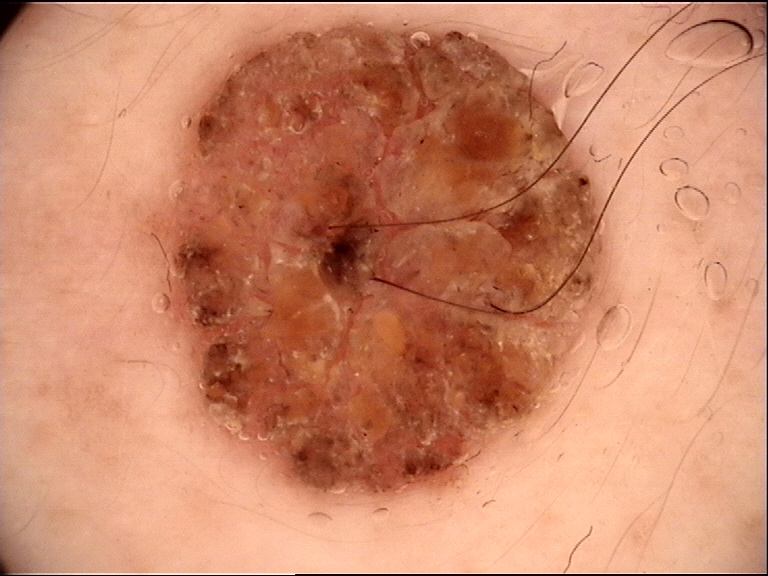Summary: A dermoscopic image of a skin lesion. The morphology is that of a banal lesion. Impression: Labeled as a dermal nevus.